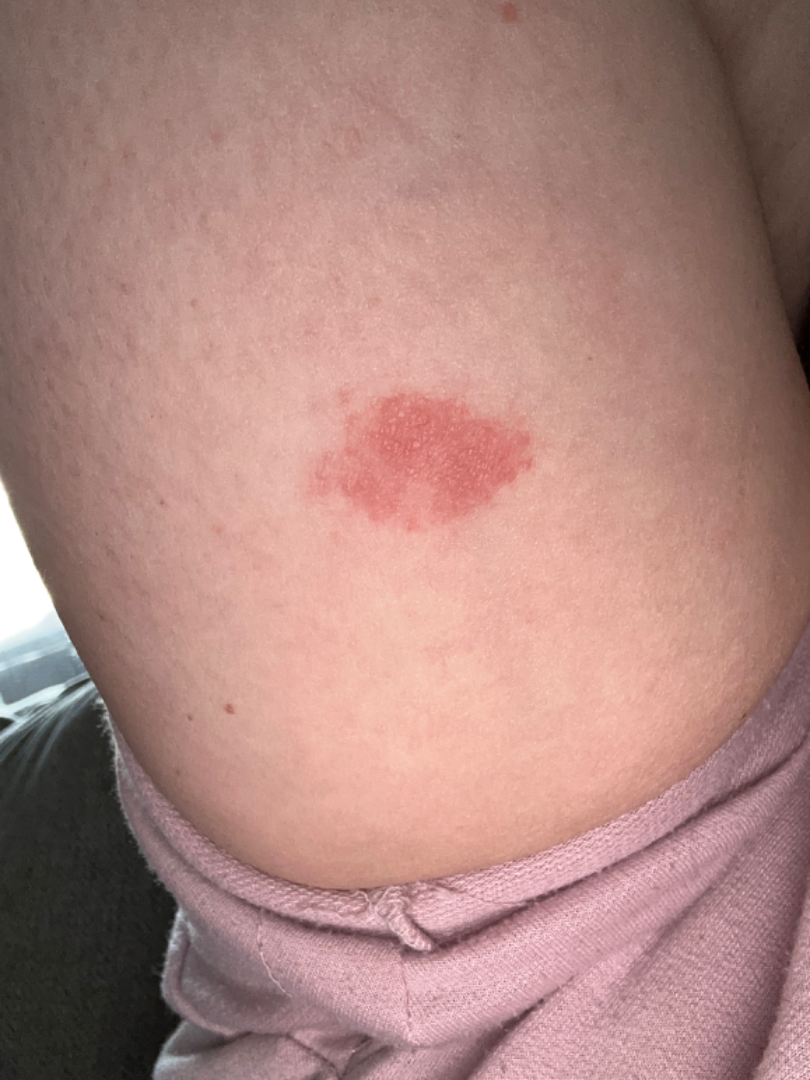The differential is split between Pigmented purpuric eruption, Eczema and Allergic Contact Dermatitis.